This is a close-up image · the patient also reports fatigue · the patient described the issue as a rash · the lesion involves the back of the torso and front of the torso · the subject is 18–29, female · reported duration is one to four weeks · the contributor notes the lesion is rough or flaky and flat · reported lesion symptoms include itching.
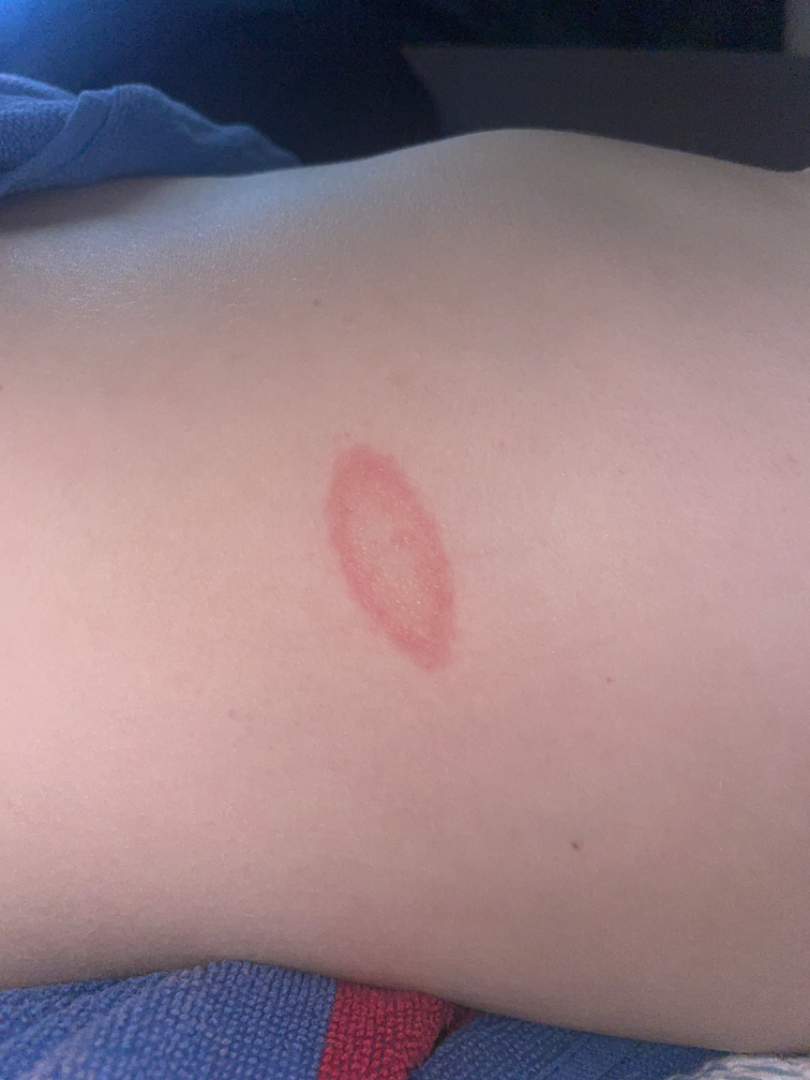| key | value |
|---|---|
| dermatologist impression | Pityriasis rosea (favored); Erythema annulare centrifugum (lower probability); Tinea (lower probability); Granuloma annulare (lower probability) |